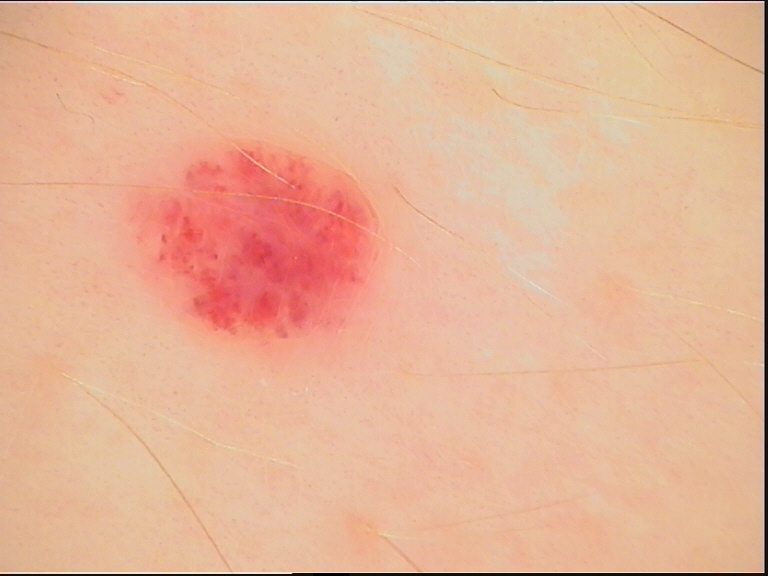Q: What is the imaging modality?
A: dermatoscopy
Q: What is the diagnosis?
A: hemangioma (expert consensus)